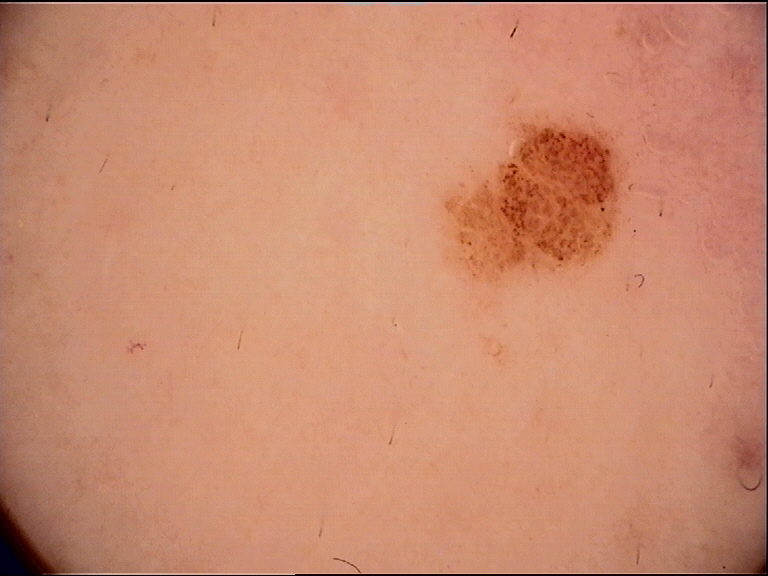A dermatoscopic image of a skin lesion. The diagnosis was a benign lesion — a dysplastic junctional nevus.